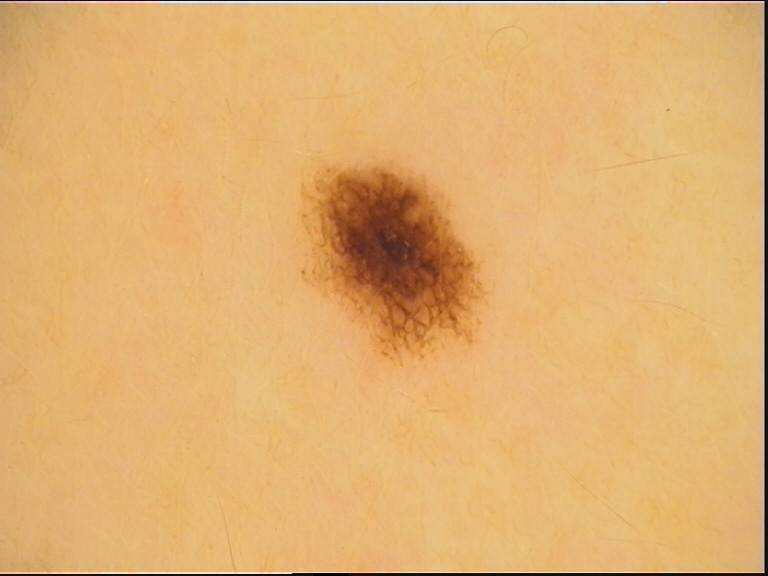image type: dermoscopy; assessment: dysplastic junctional nevus (expert consensus).